The lesion involves the head or neck. An image taken at an angle. The lesion is described as raised or bumpy and rough or flaky. The patient reports the condition has been present for more than one year. The contributor is a male aged 50–59.
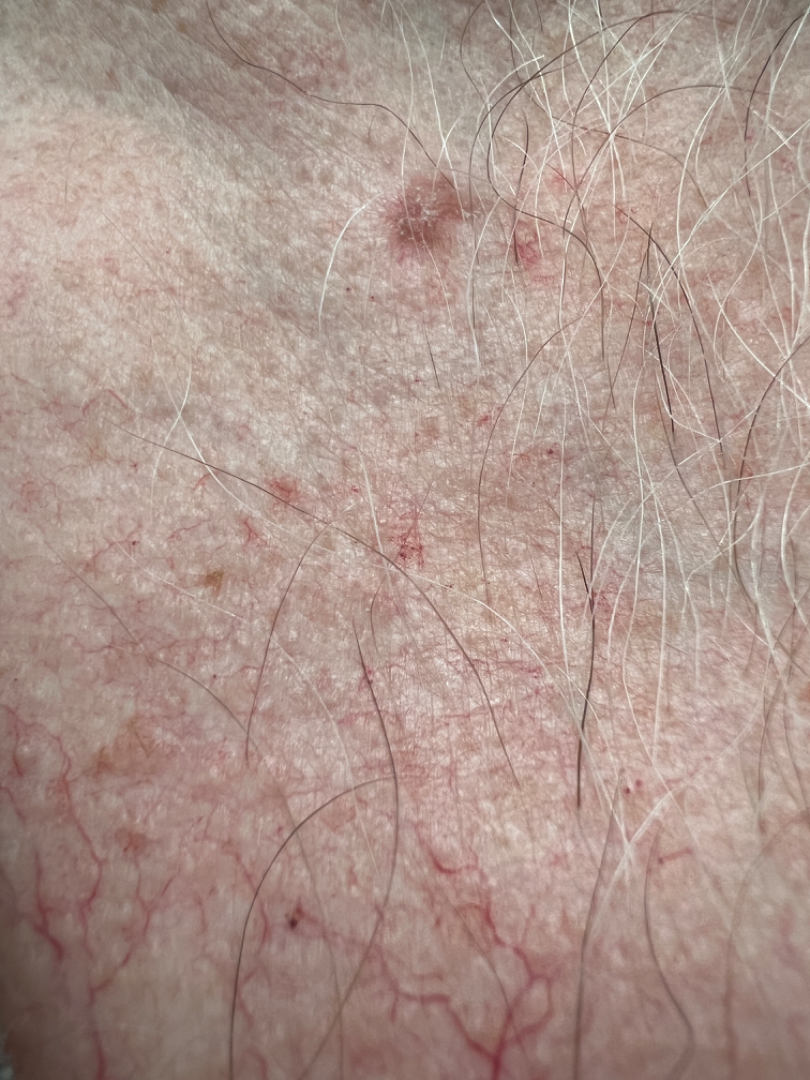Single-reviewer assessment: the differential is split between Actinic Keratosis, Basal Cell Carcinoma and SCC/SCCIS.